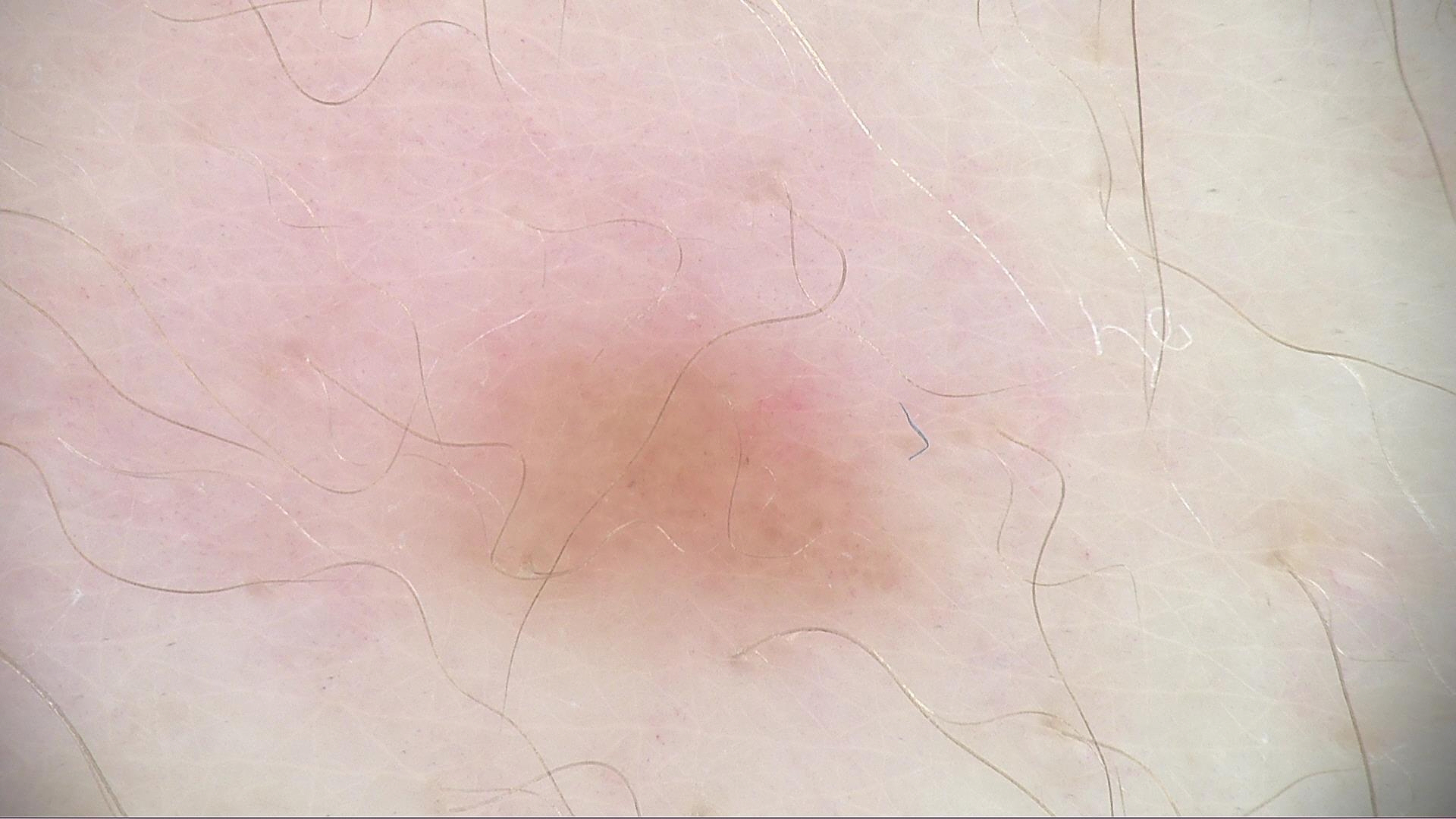Q: What kind of image is this?
A: dermatoscopy
Q: How is the lesion classified?
A: banal
Q: What is this lesion?
A: junctional nevus (expert consensus)